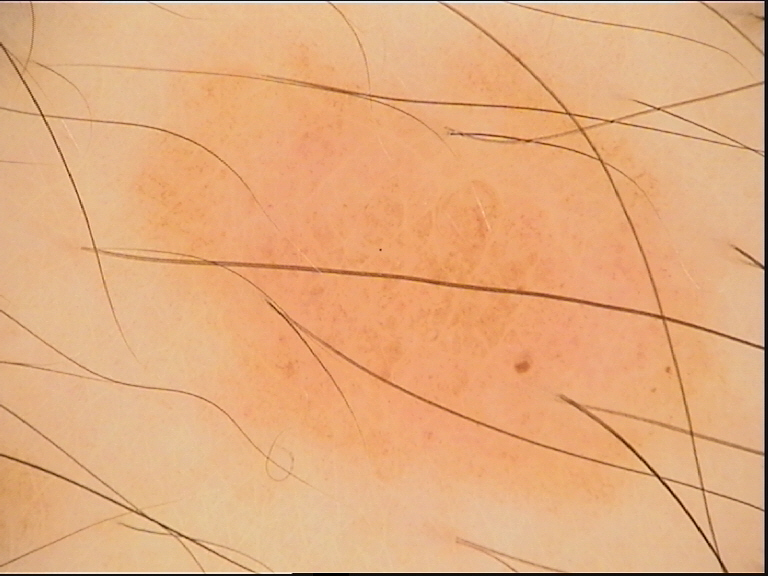A skin lesion imaged with a dermatoscope.
The diagnostic label was a dysplastic junctional nevus.